The photograph was taken at a distance, the affected area is the back of the hand, the patient is male — 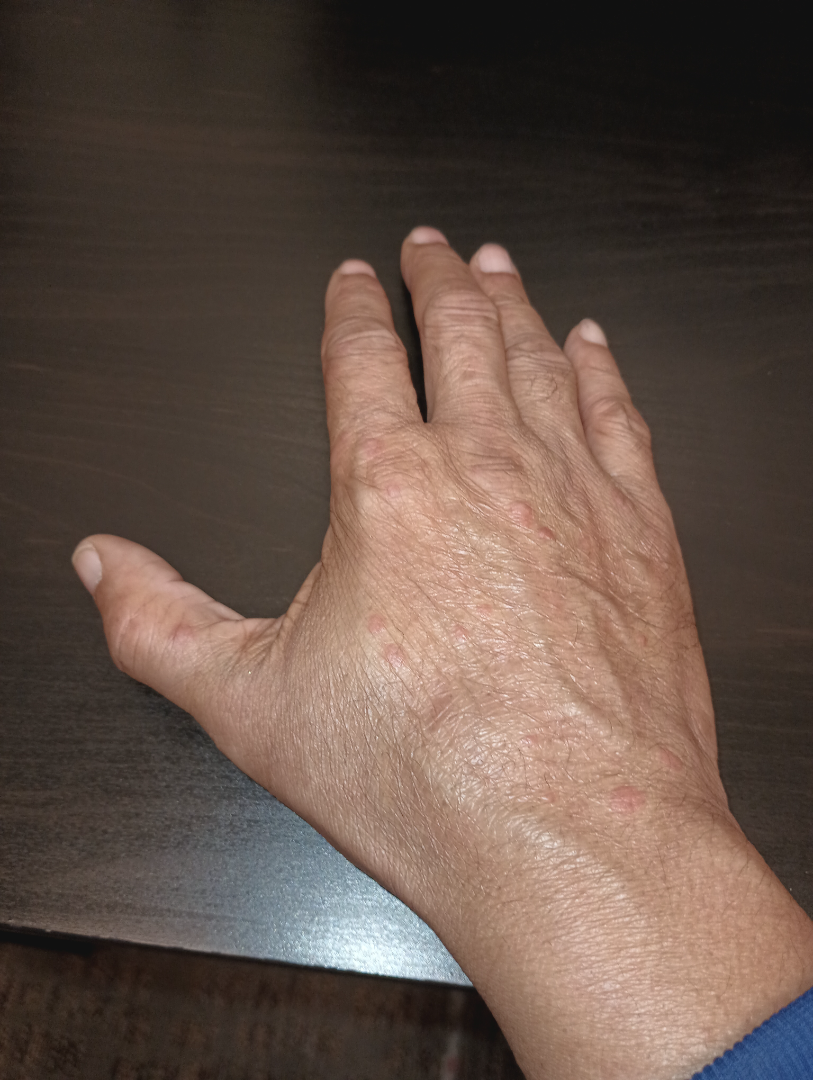The reviewing dermatologists' impression was: Granuloma annulare and Insect Bite were each considered, in no particular order; a remote consideration is Verruca vulgaris; lower on the differential is Cutaneous sarcoidosis.